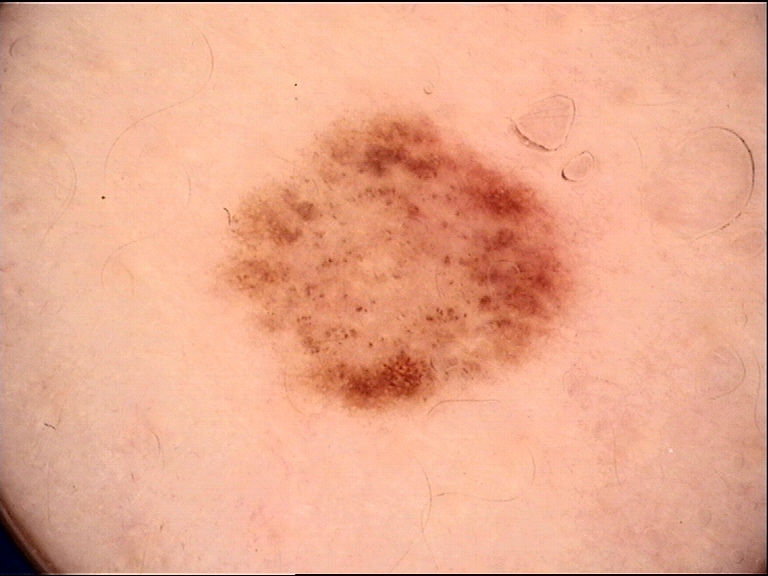Conclusion:
Classified as a dysplastic junctional nevus.